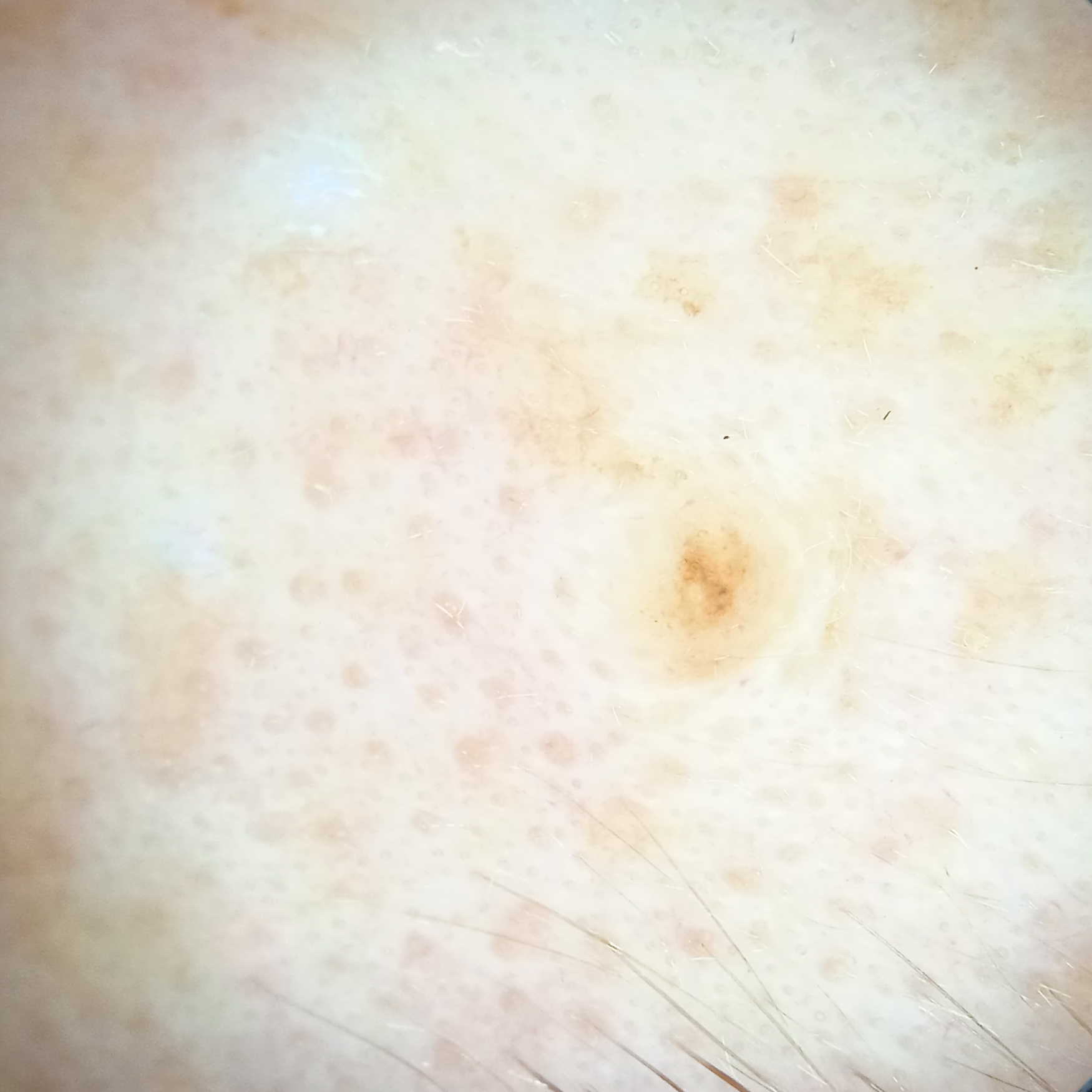A female patient 50 years of age.
Dermoscopy of a skin lesion.
The referring clinician suspected melanoma.
The lesion is located on the face.
The lesion measures approximately 1.8 mm.
The consensus diagnosis for this lesion was a melanocytic nevus.